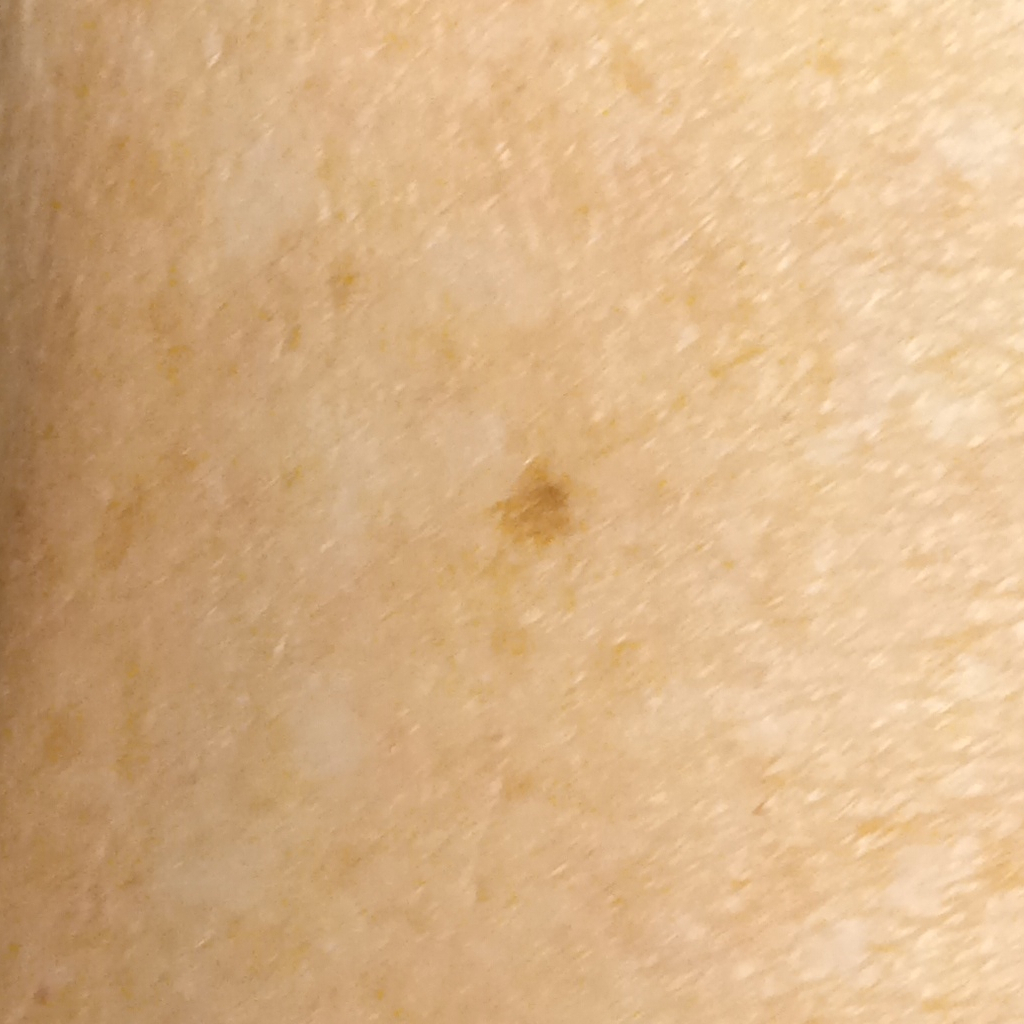The dermatologists' assessment was a melanocytic nevus.